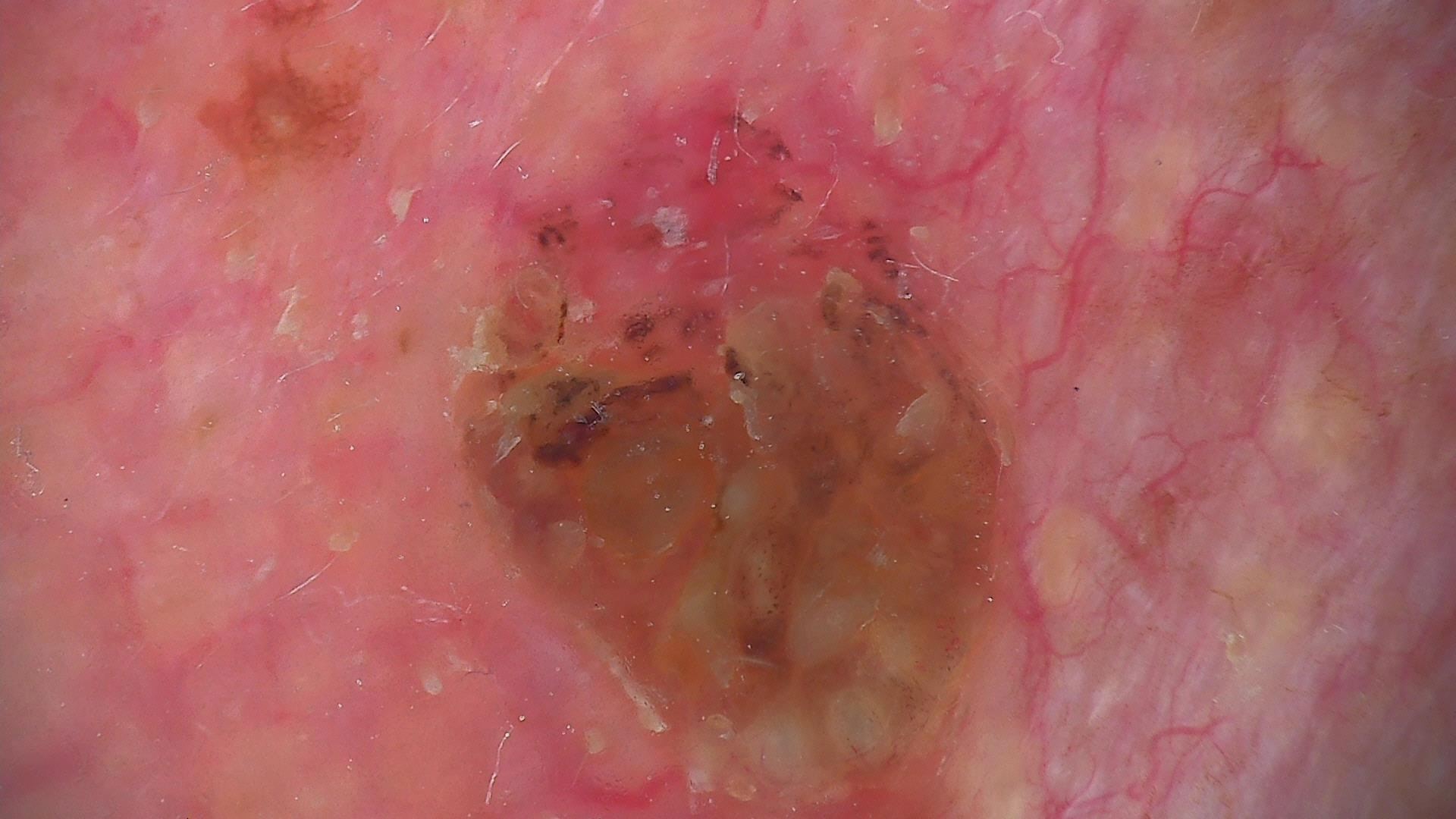Summary: A dermoscopy image of a single skin lesion. The morphology is that of a keratinocytic lesion. Conclusion: Labeled as a seborrheic keratosis.